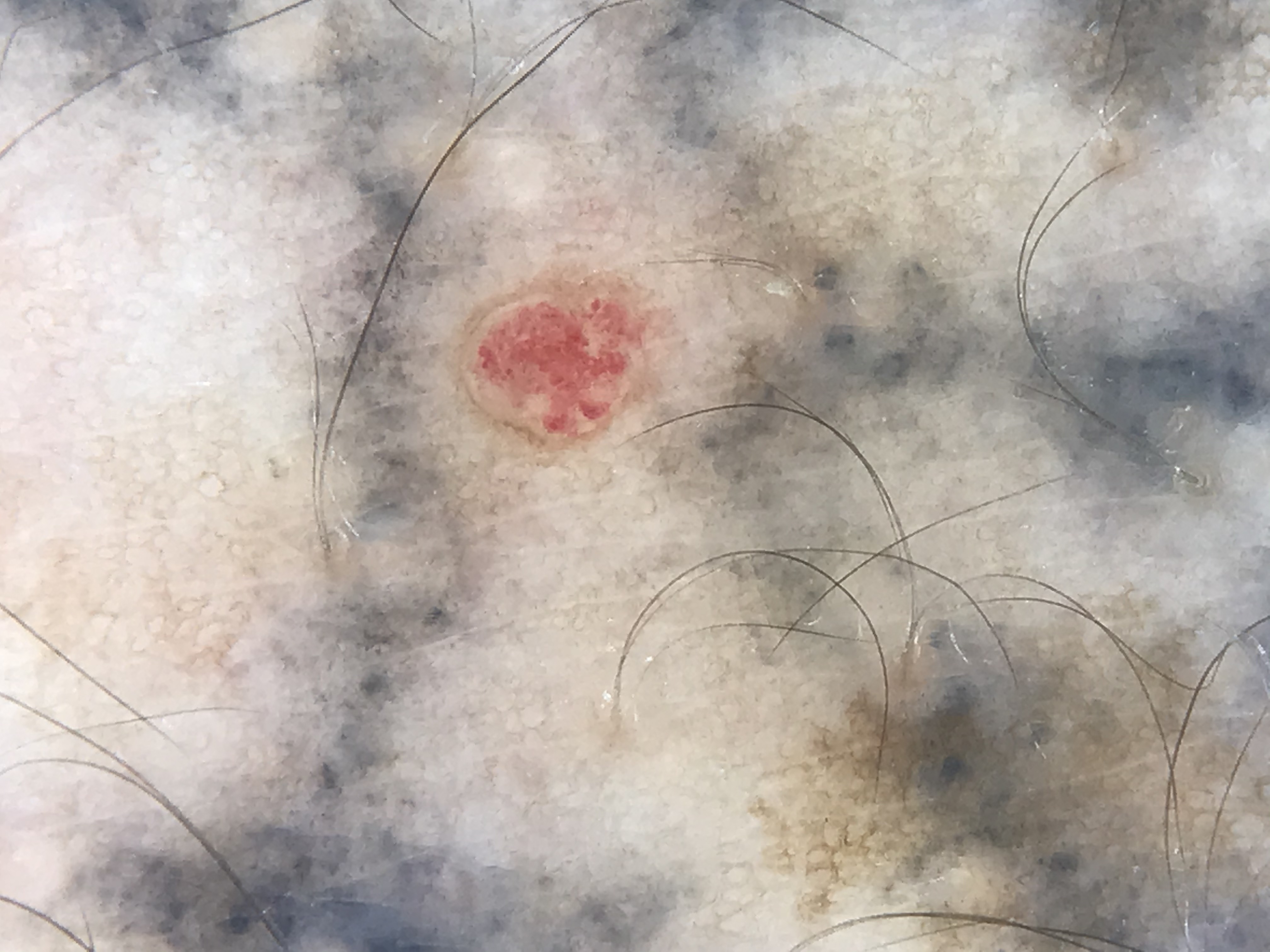modality: dermoscopy | label: hemangioma (expert consensus).